A dermatoscopic image of a skin lesion.
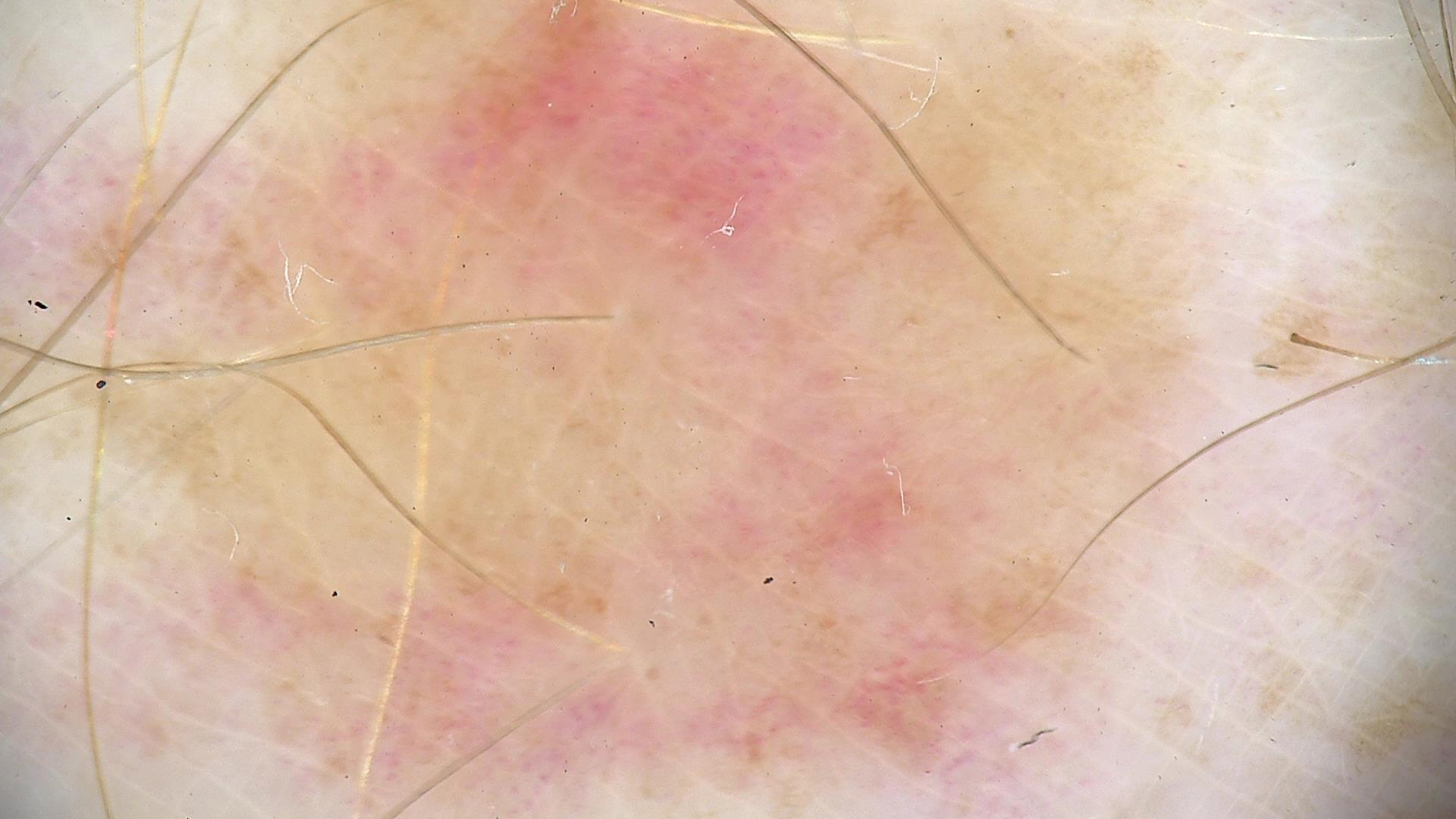Findings:
* label: dysplastic junctional nevus (expert consensus)